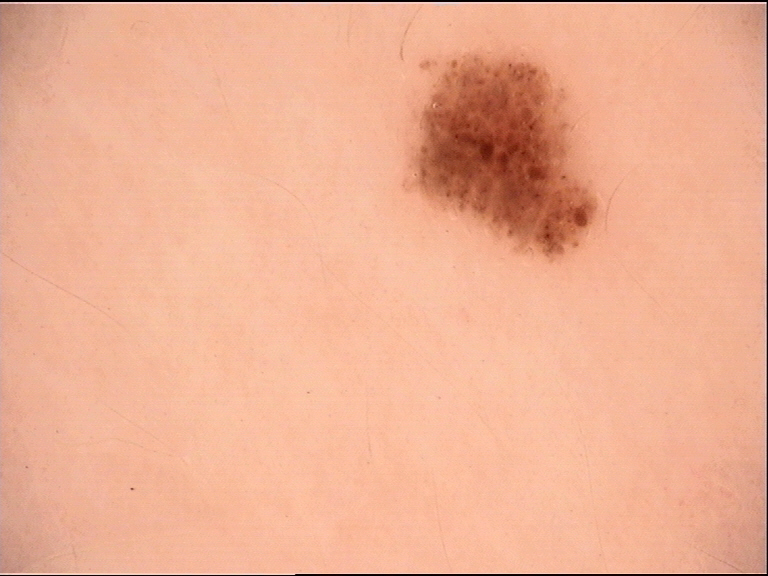Summary:
A dermoscopic photograph of a skin lesion.
Conclusion:
Consistent with a benign lesion — a dysplastic junctional nevus.